A dermoscopy image of a single skin lesion:
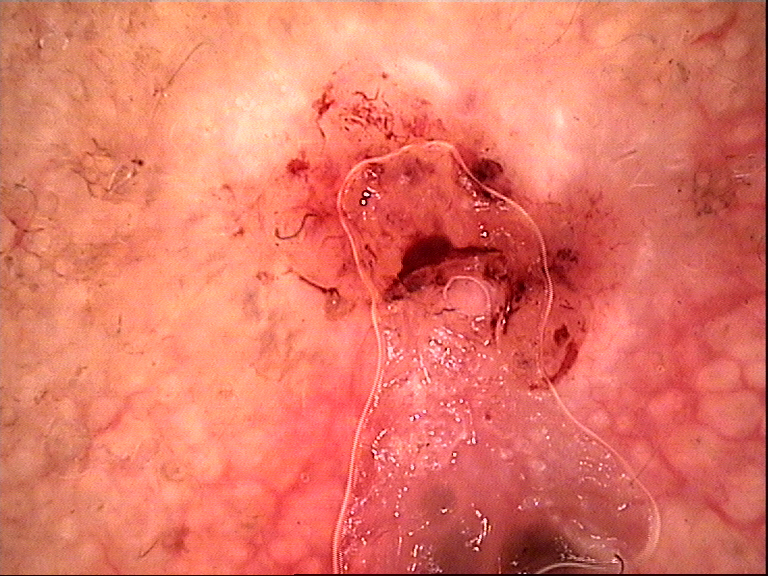This is a keratinocytic lesion.
The biopsy diagnosis was a basal cell carcinoma.